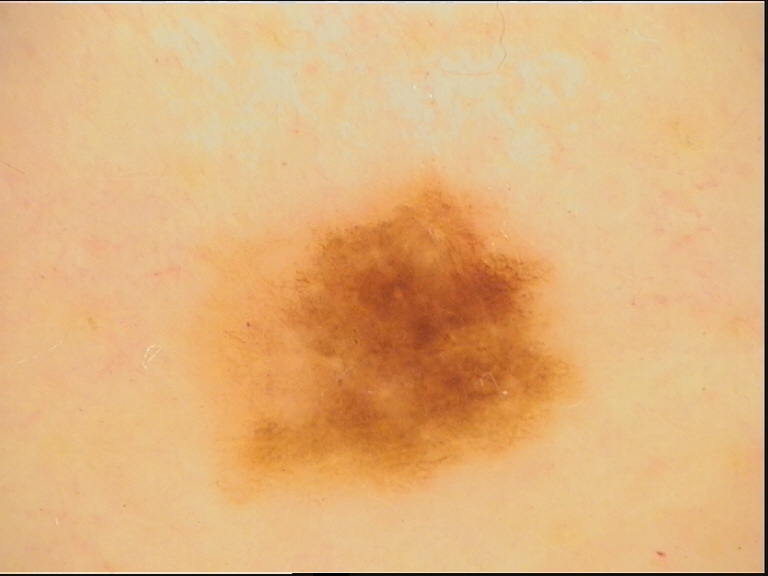Impression:
Diagnosed as a benign lesion — a dysplastic junctional nevus.